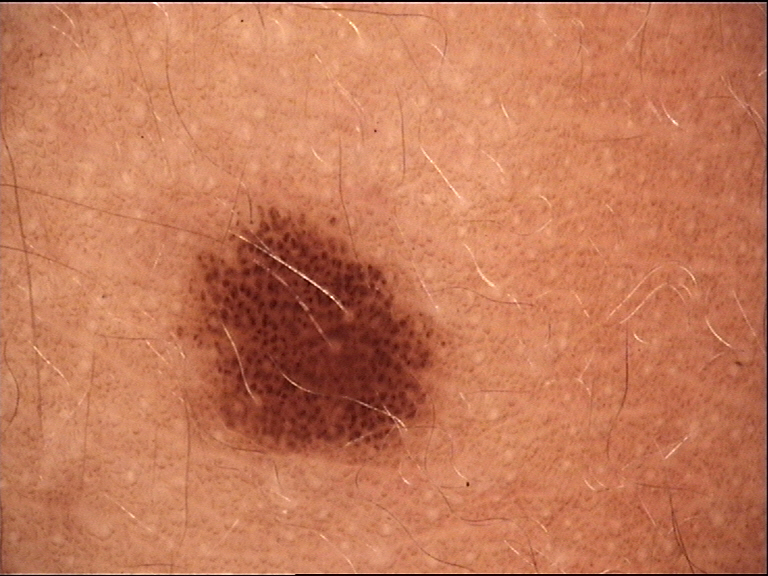The architecture is that of a banal lesion.
Diagnosed as a junctional nevus.